Located on the leg; an image taken at a distance; the lesion is described as rough or flaky; no relevant lesion symptoms reported; present for one to four weeks.
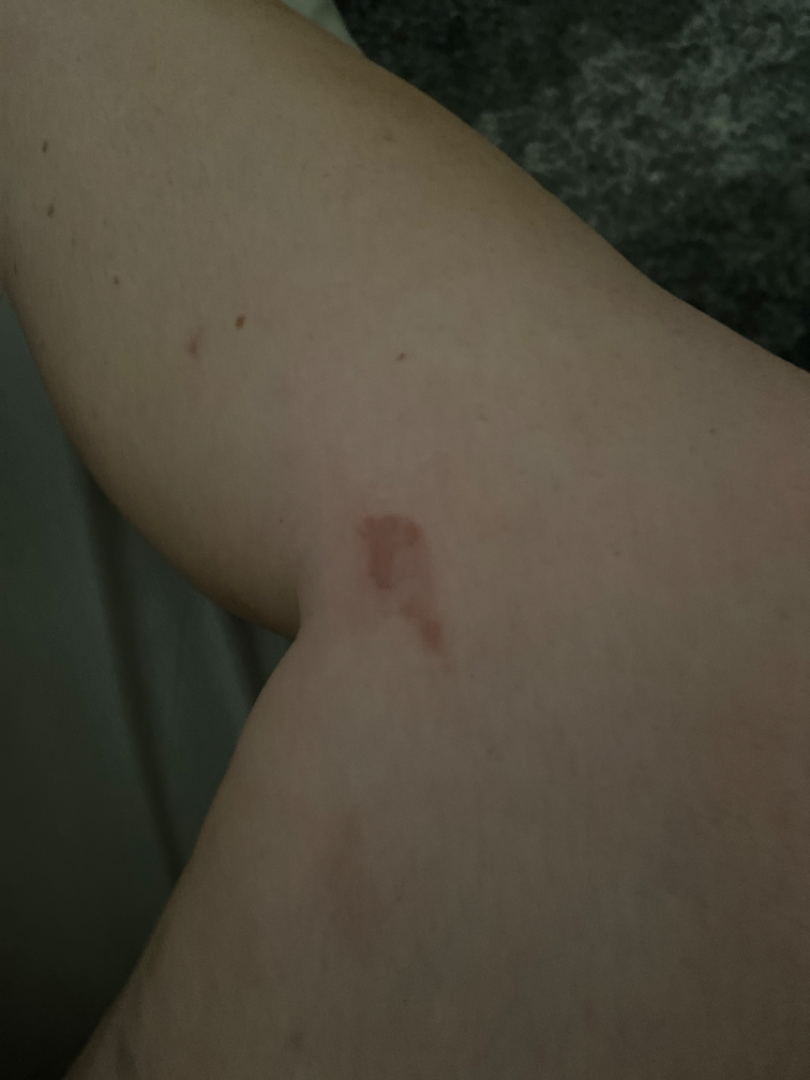Q: Could the case be diagnosed?
A: indeterminate